An image taken at a distance; the affected area is the head or neck: 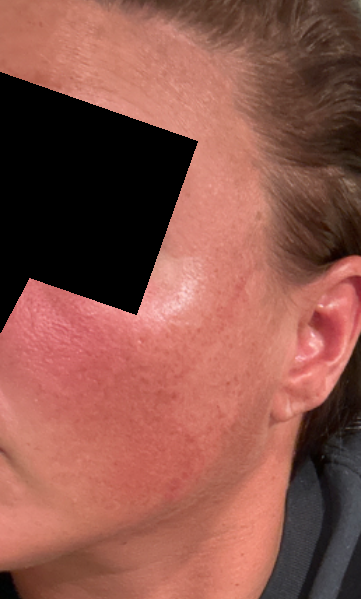lesion texture: flat
patient describes the issue as: a rash
clinical impression: most consistent with Melasma